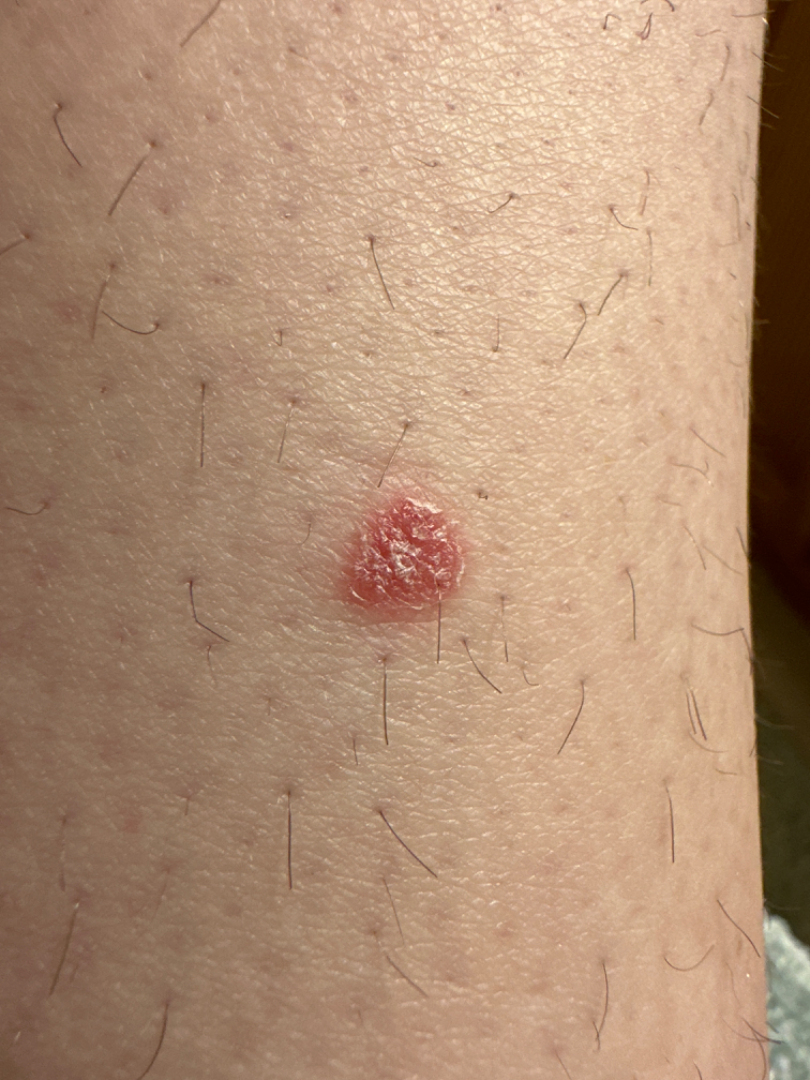image framing: close-up | body site: leg | impression: the differential is split between Psoriasis, SCC/SCCIS and Basal Cell Carcinoma.